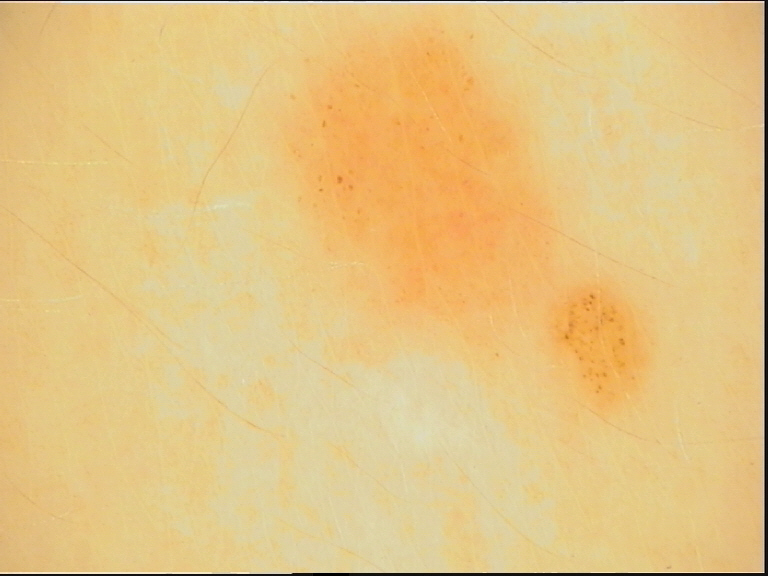A dermoscopic photograph of a skin lesion. Consistent with a benign lesion — a dysplastic junctional nevus.